This is a close-up image. The subject is female. The arm is involved — 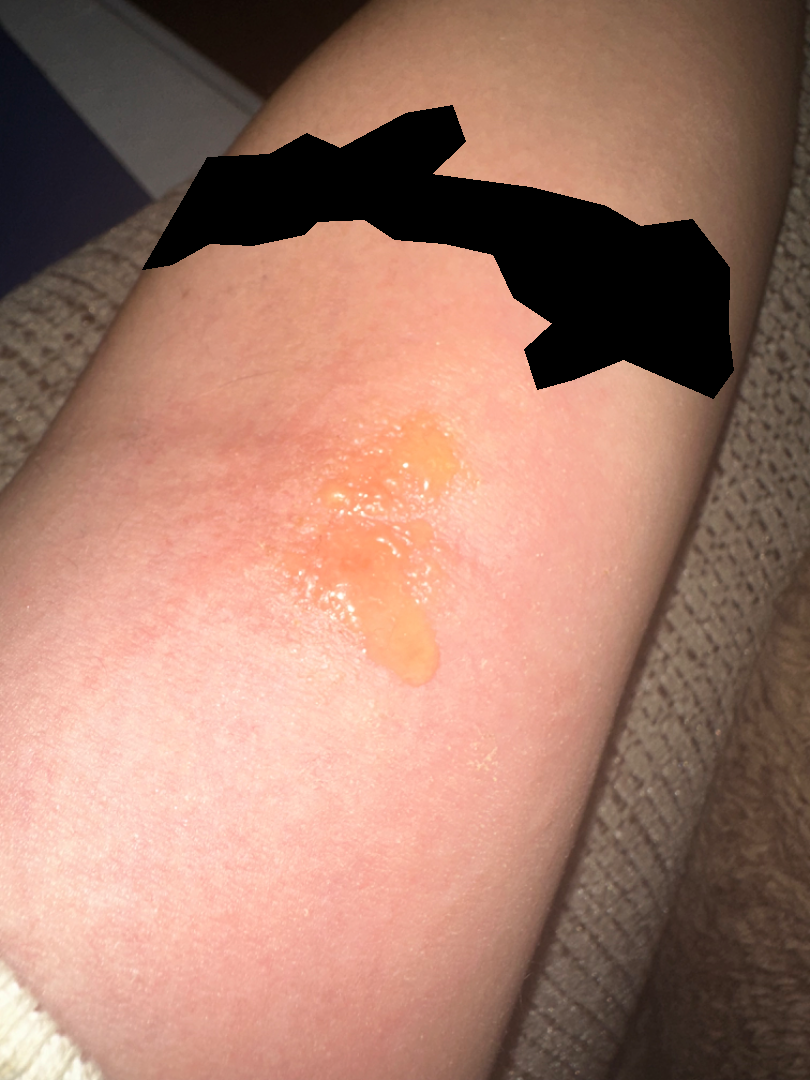impression — the leading consideration is Eczema; the differential also includes Allergic Contact Dermatitis.